A clinical close-up of a skin lesion · collected as part of a research study, without a referral diagnosis · a female patient age 26:
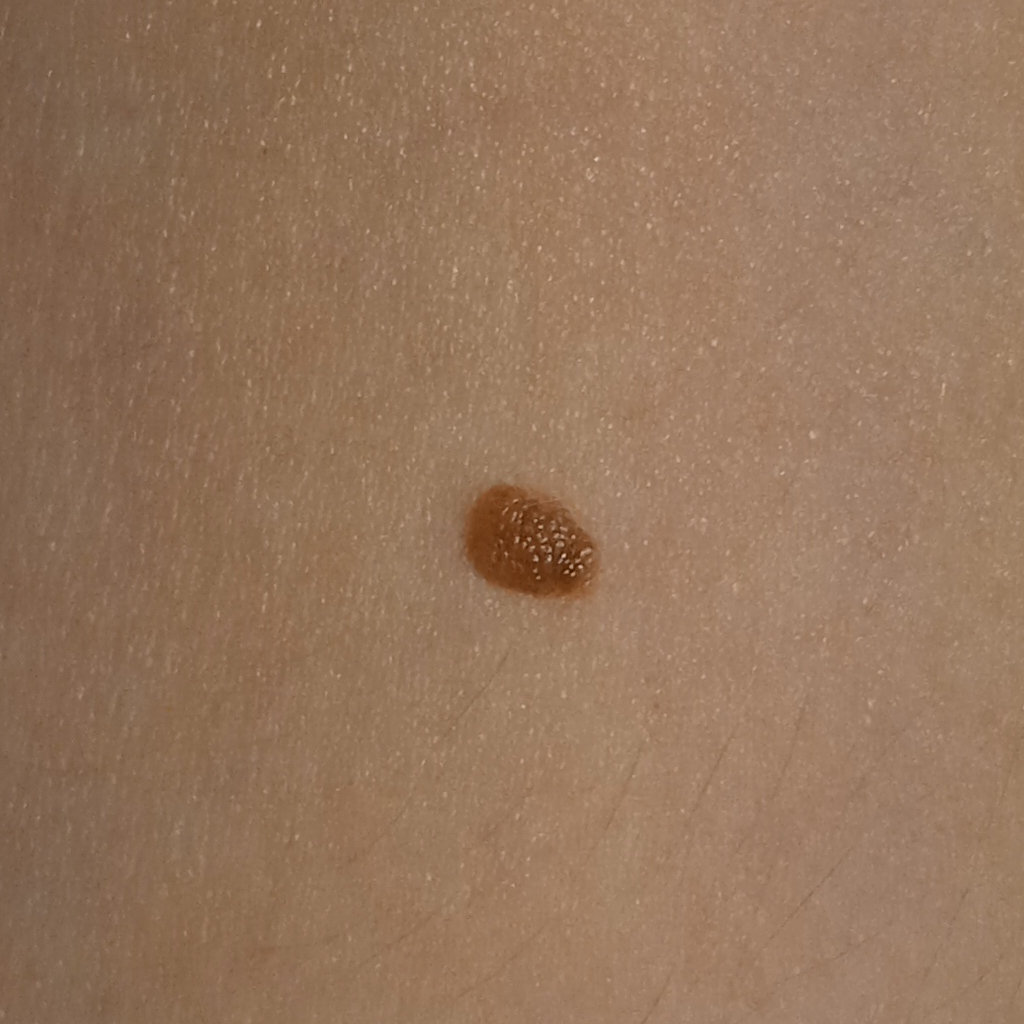The lesion involves an arm. The lesion measures approximately 5.5 mm. Dermatologist review favored a melanocytic nevus.